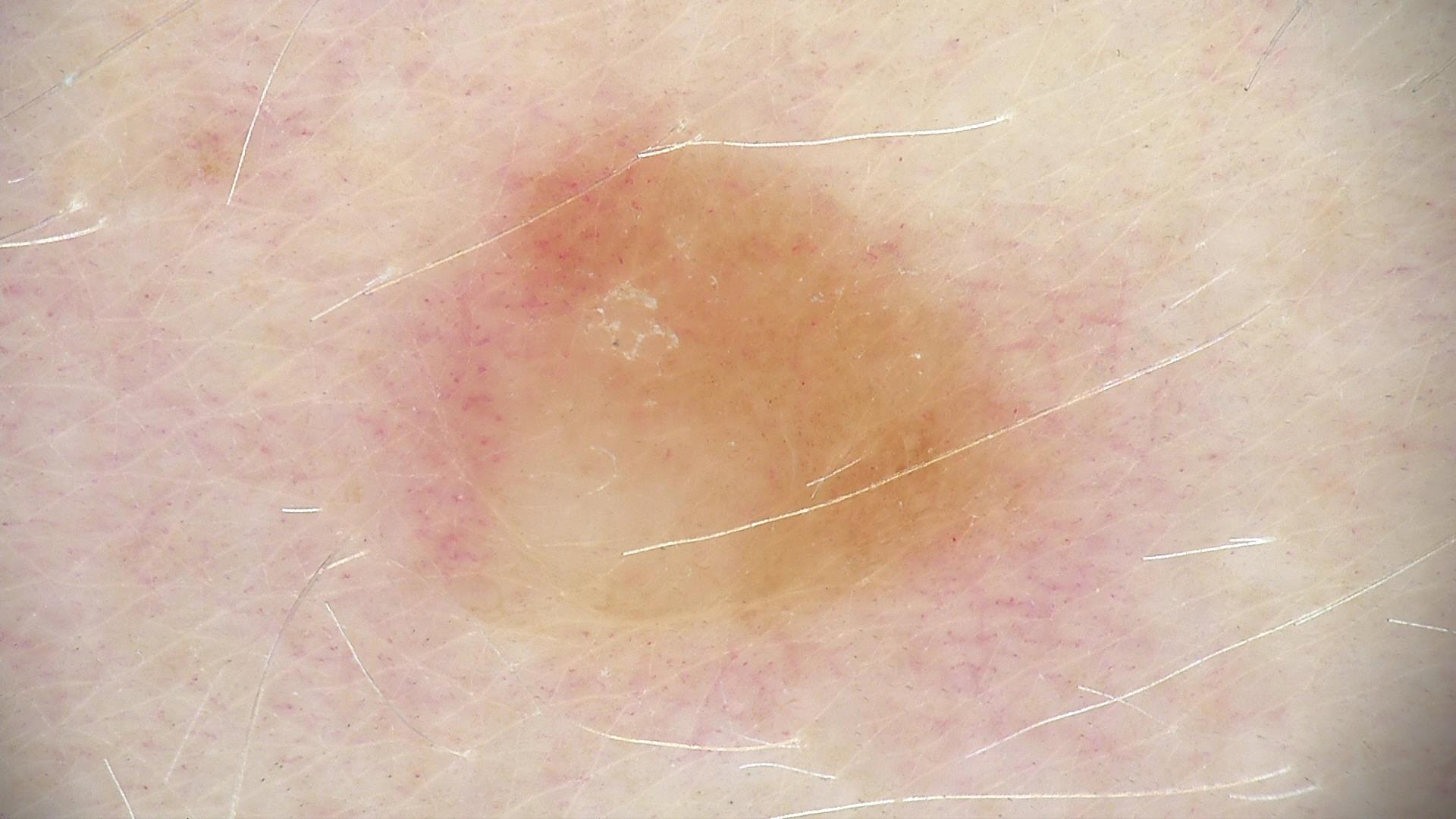Q: What kind of image is this?
A: dermatoscopy
Q: What was the diagnostic impression?
A: dermal nevus (expert consensus)